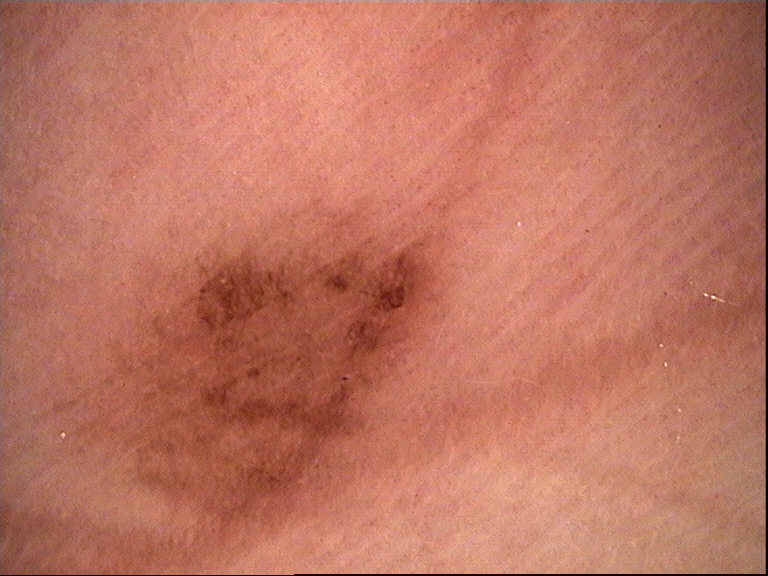Classified as an acral dysplastic junctional nevus.